A dermoscopic photograph of a skin lesion.
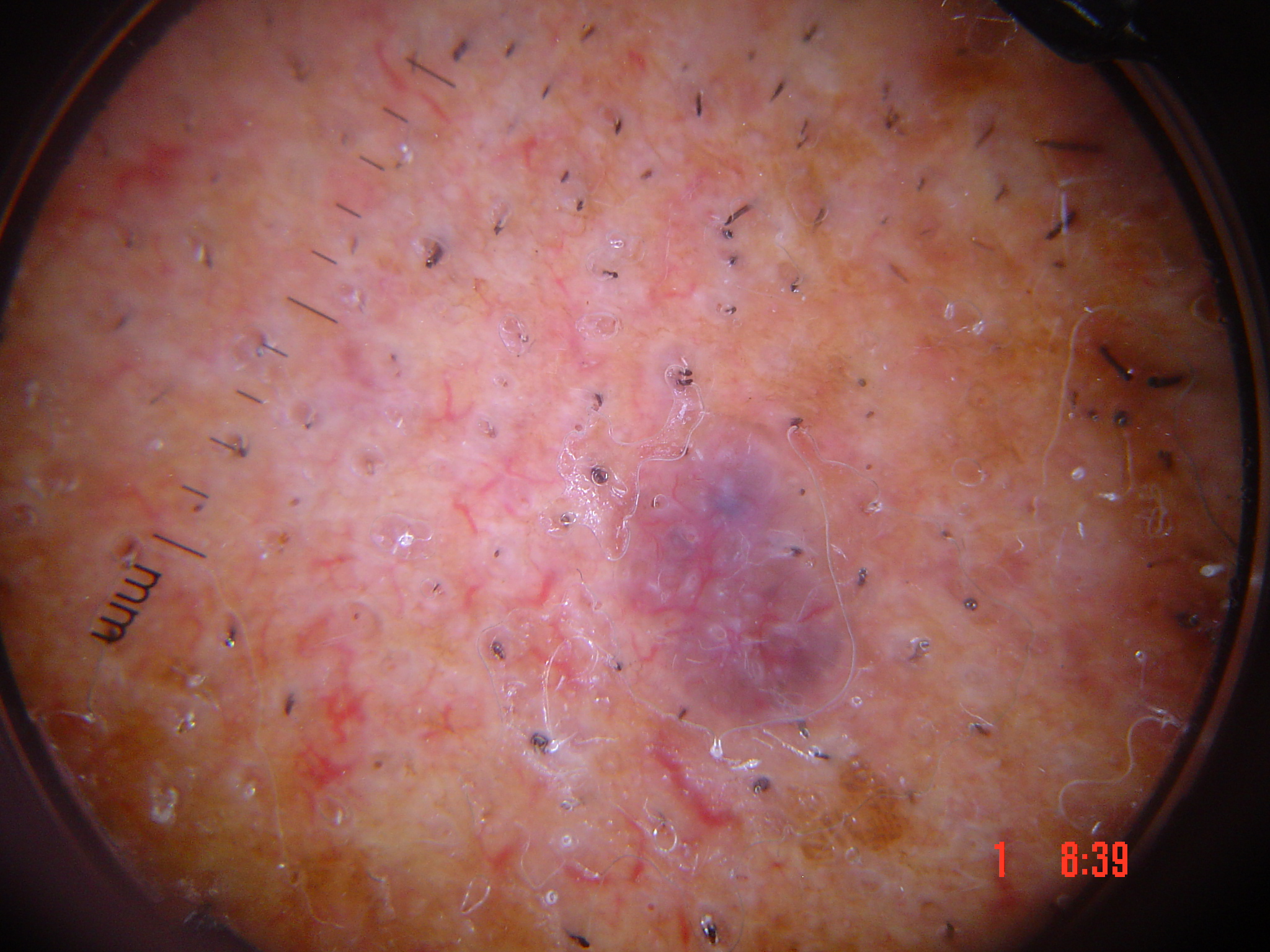Findings:
• lesion type · keratinocytic
• diagnosis · basal cell carcinoma (biopsy-proven)